Dermoscopy of a skin lesion.
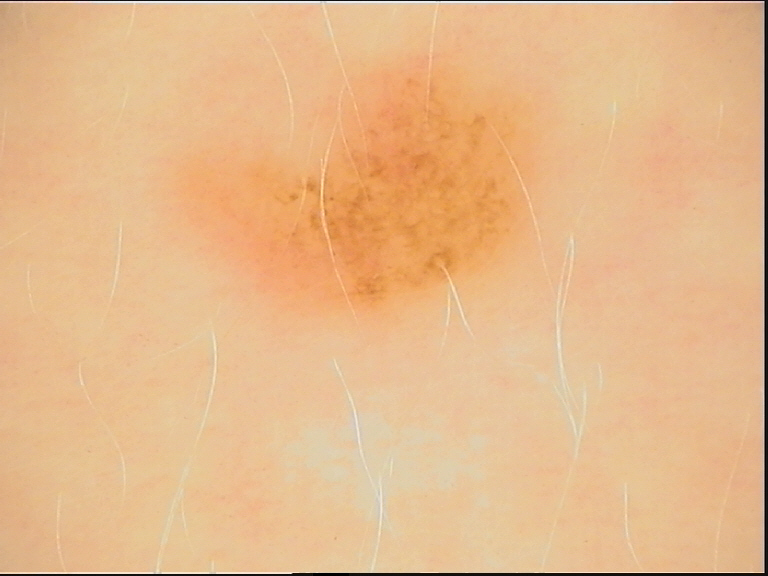{
  "diagnosis": {
    "name": "dysplastic junctional nevus",
    "code": "jd",
    "malignancy": "benign",
    "super_class": "melanocytic",
    "confirmation": "expert consensus"
  }
}